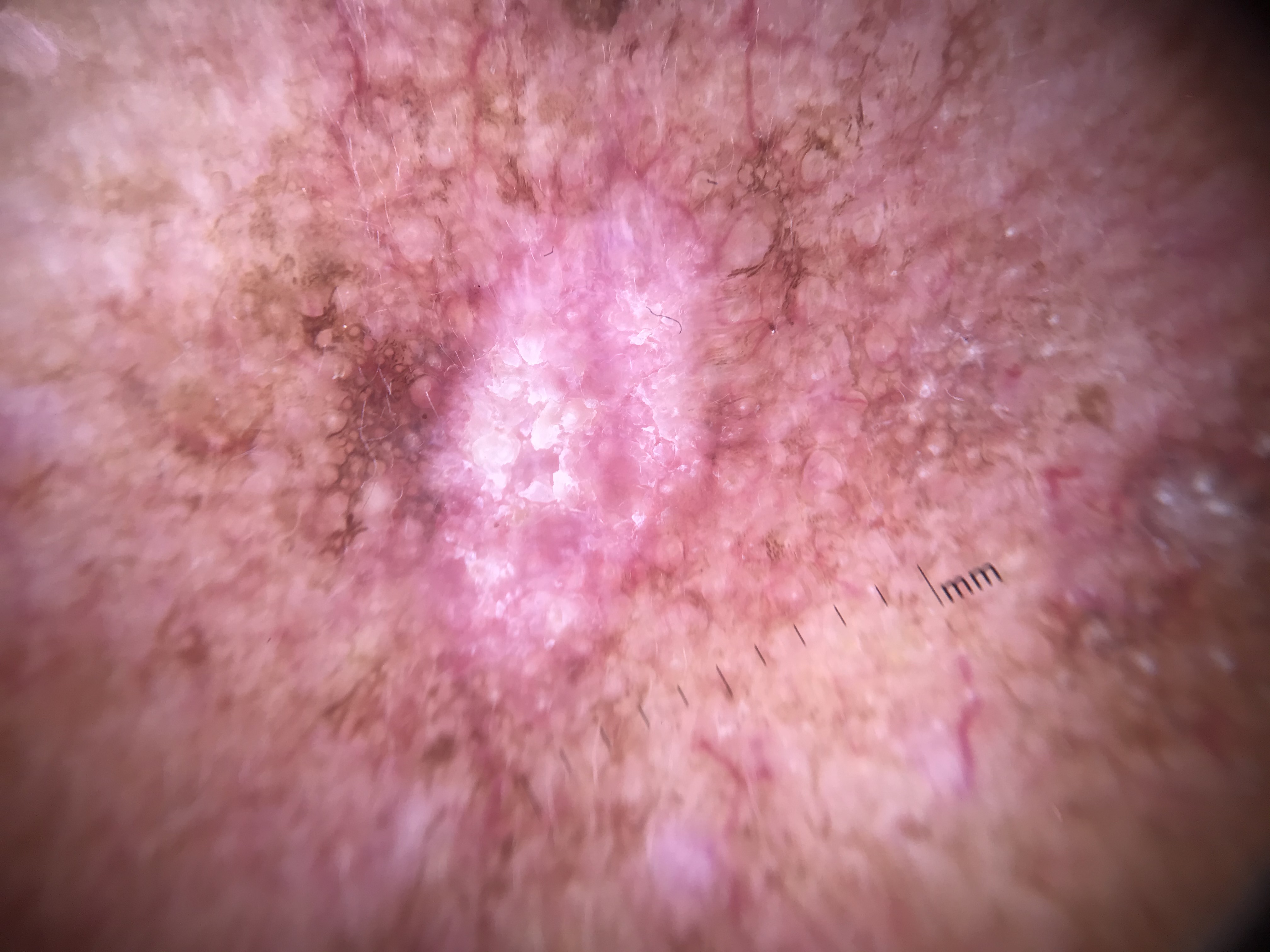image — dermatoscopy; category — keratinocytic; label — squamous cell carcinoma (biopsy-proven).